The photo was captured at a distance: 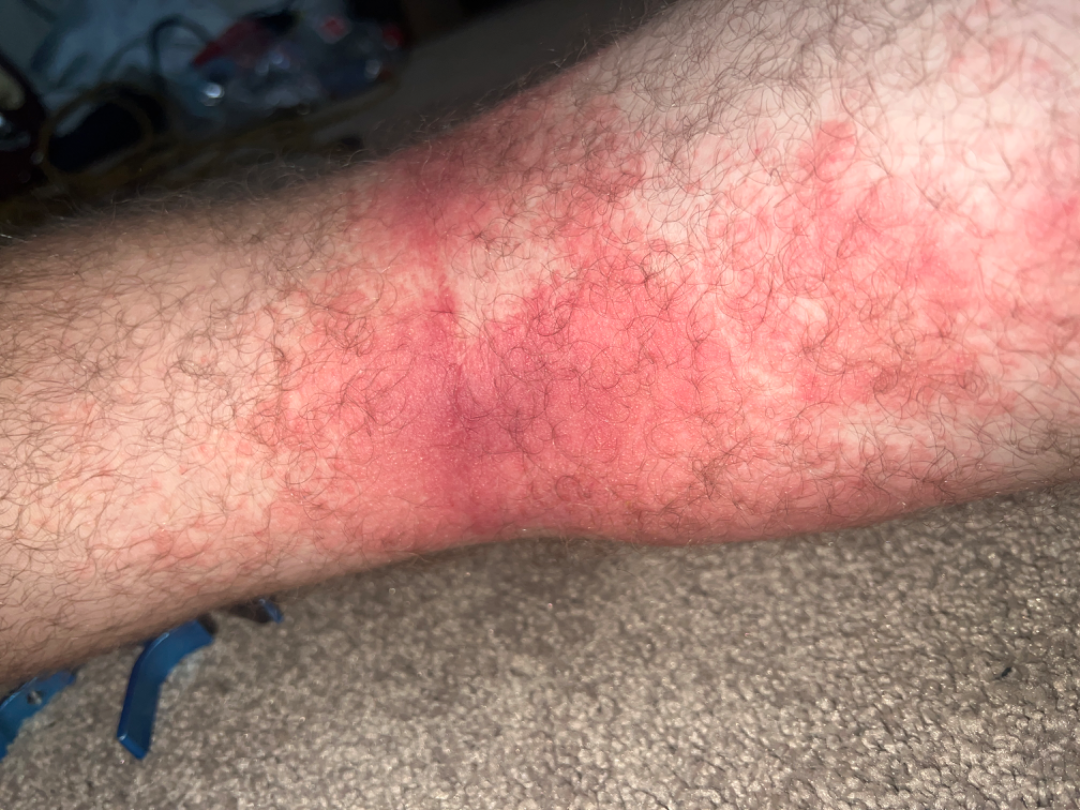Review: On teledermatology review: Allergic Contact Dermatitis (weight 0.67); Eczema (weight 0.33).